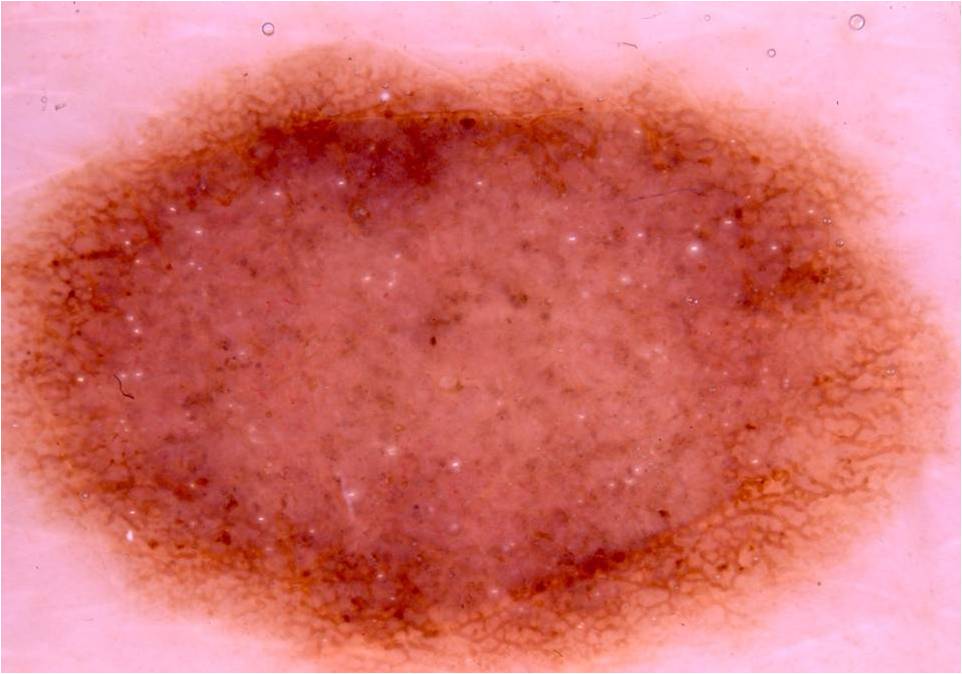A dermoscopy image of a single skin lesion.
Dermoscopic assessment notes globules, pigment network, and milia-like cysts.
The lesion stretches across essentially the whole frame.
The clinical diagnosis was a melanocytic nevus.